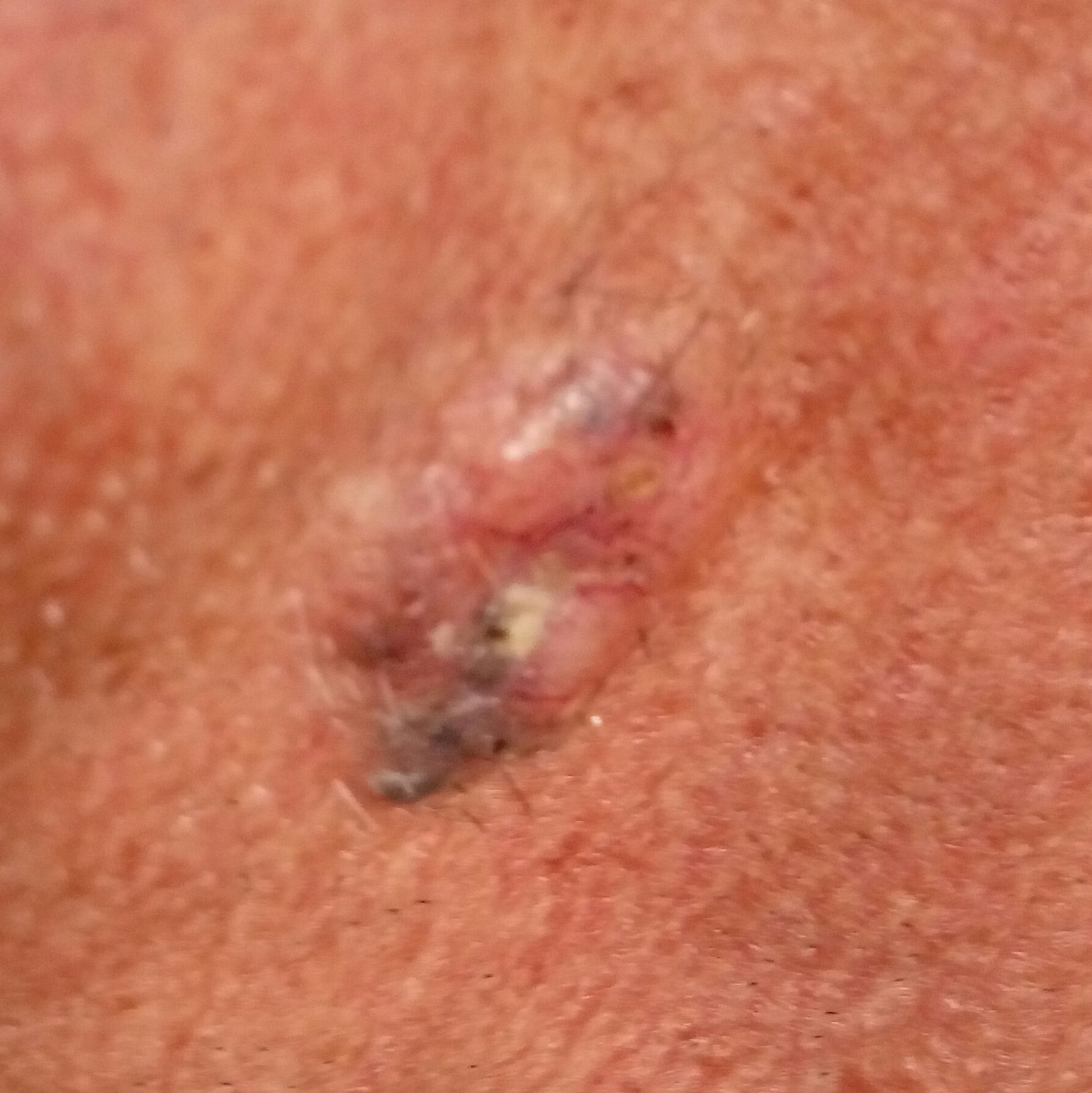patient = male, age 59
imaging = clinical photograph
location = the neck
symptoms = growth, bleeding, pain, elevation, itching
diagnosis = basal cell carcinoma (biopsy-proven)